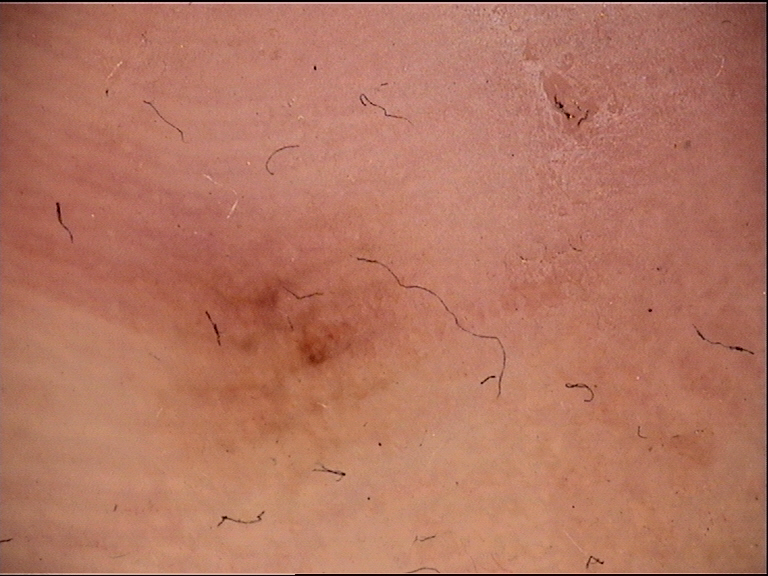Q: What kind of image is this?
A: dermatoscopy
Q: What was the diagnostic impression?
A: acral dysplastic junctional nevus (expert consensus)